Female subject, age 30–39; texture is reported as fluid-filled and raised or bumpy; the condition has been present for more than one year; reported lesion symptoms include bothersome appearance, pain, darkening, burning and itching; located on the arm, back of the torso, head or neck and back of the hand; the photograph was taken at a distance; associated systemic symptoms include shortness of breath, joint pain, chills, mouth sores and fatigue; skin tone: FST II: 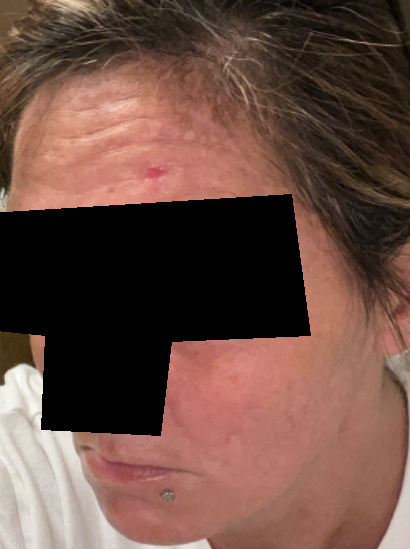differential — most consistent with Basal Cell Carcinoma; with consideration of Traumatic ulcer.